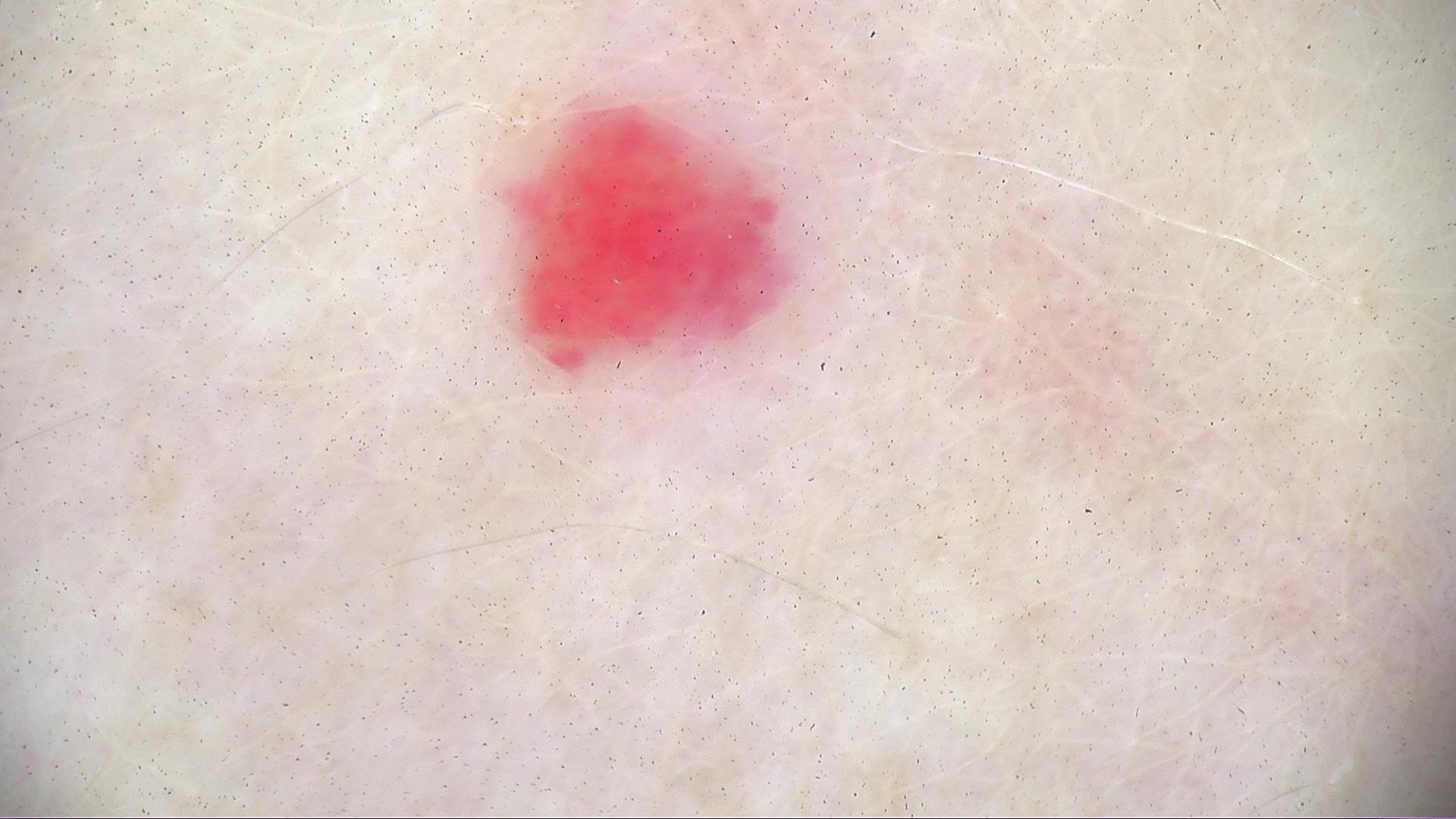Impression:
The diagnosis was a hemangioma.